Fitzpatrick skin type II · a close-up photograph · the lesion involves the top or side of the foot · the lesion is described as rough or flaky · the lesion is associated with bleeding, enlargement, bothersome appearance and itching · no associated systemic symptoms reported · the condition has been present for one to four weeks — 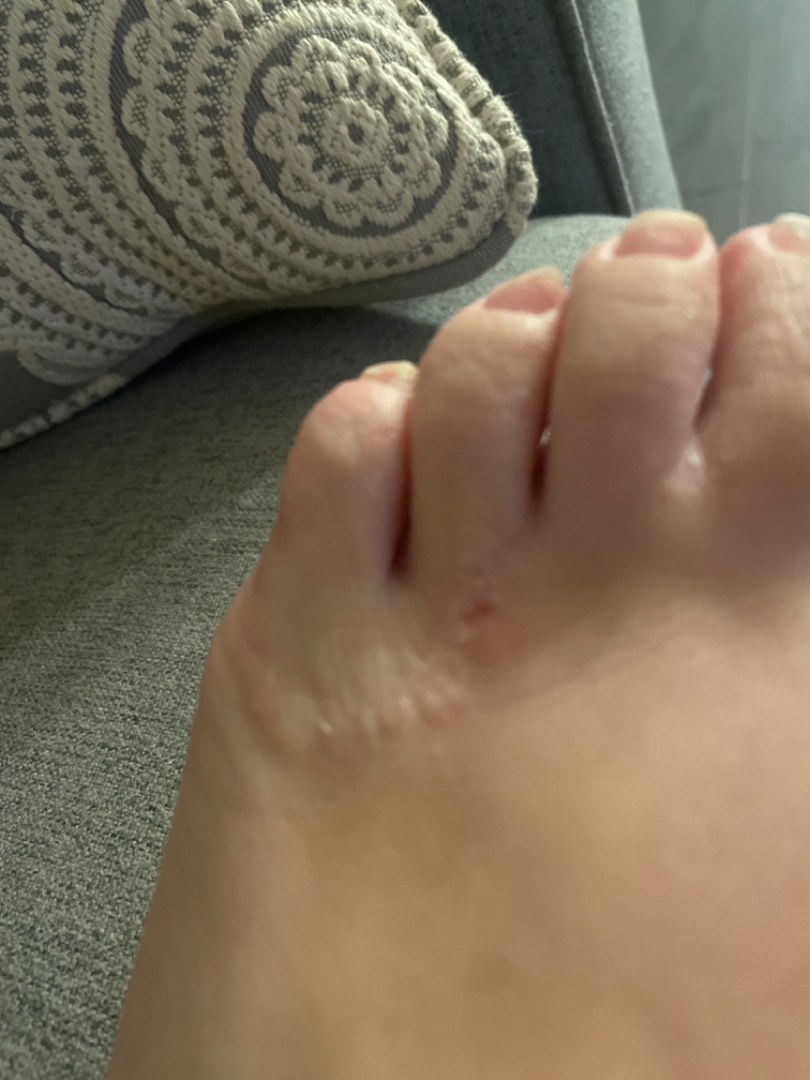assessment: unable to determine